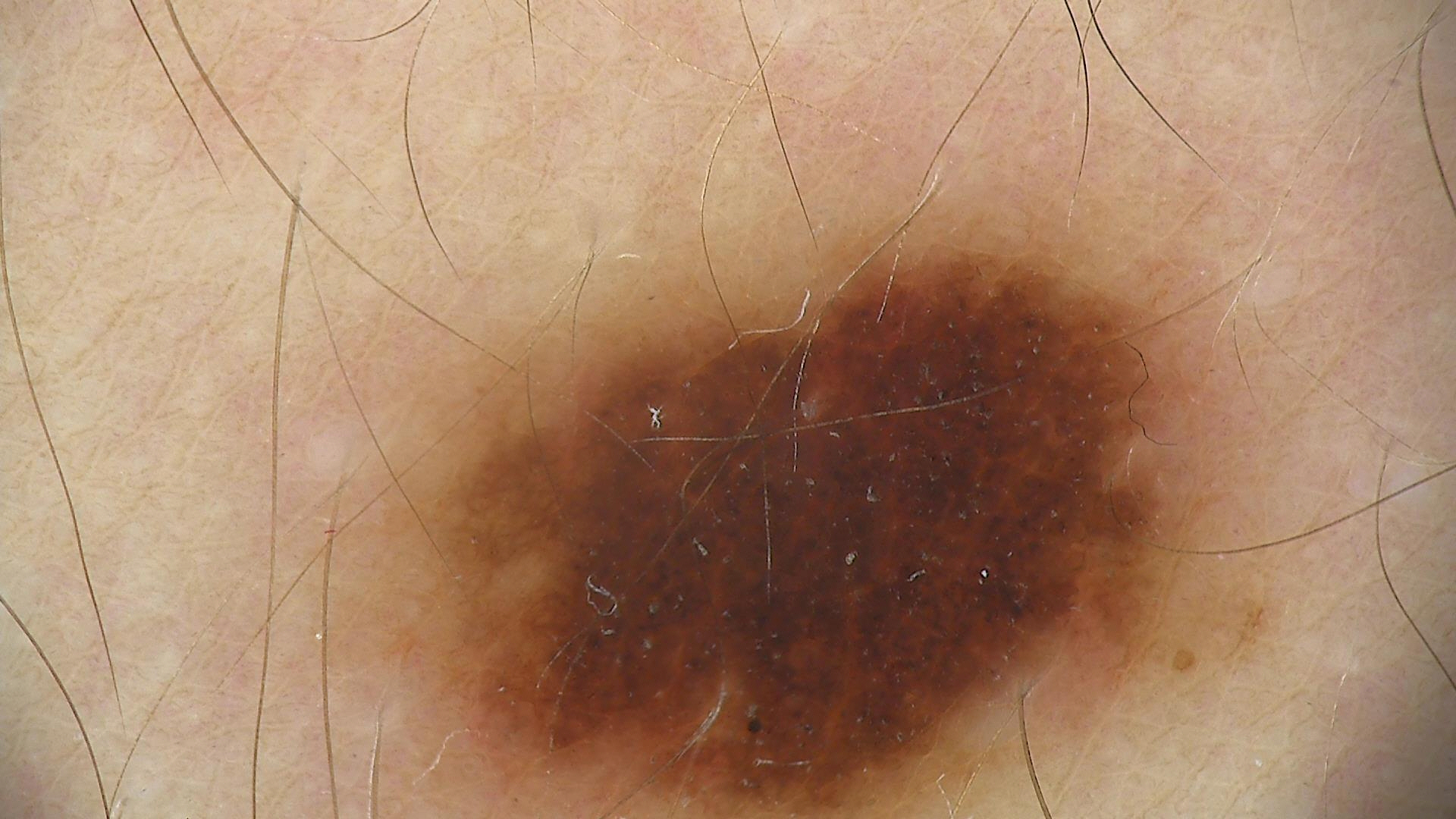Q: What kind of image is this?
A: dermoscopy
Q: What was the diagnostic impression?
A: compound nevus (expert consensus)